The patient notes the lesion is raised or bumpy and fluid-filled · an image taken at an angle · no associated systemic symptoms reported · the lesion involves the top or side of the foot · self-categorized by the patient as a rash · the patient is 30–39, male · the patient reported no relevant symptoms from the lesion · the condition has been present for about one day — 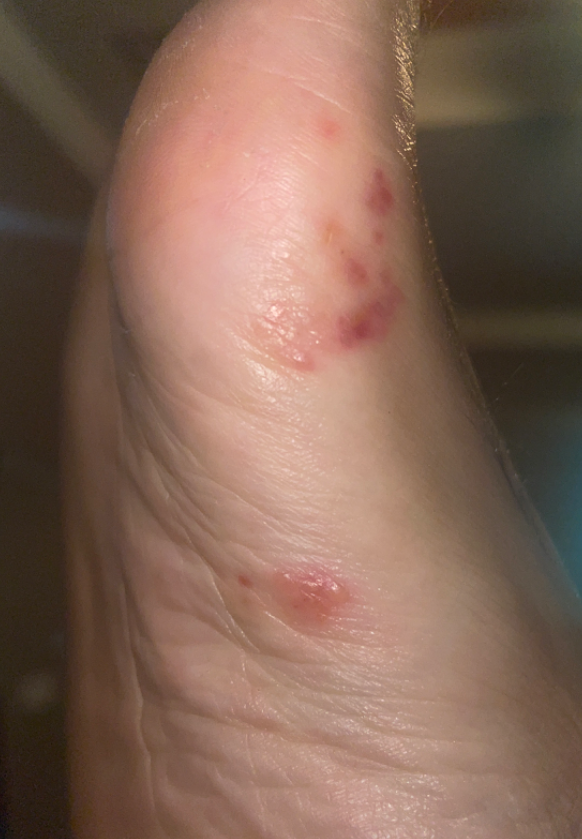– impression: Eczema (favored); Herpes Zoster (considered); Cutaneous larva migrans (considered)